A skin lesion imaged with a dermatoscope: 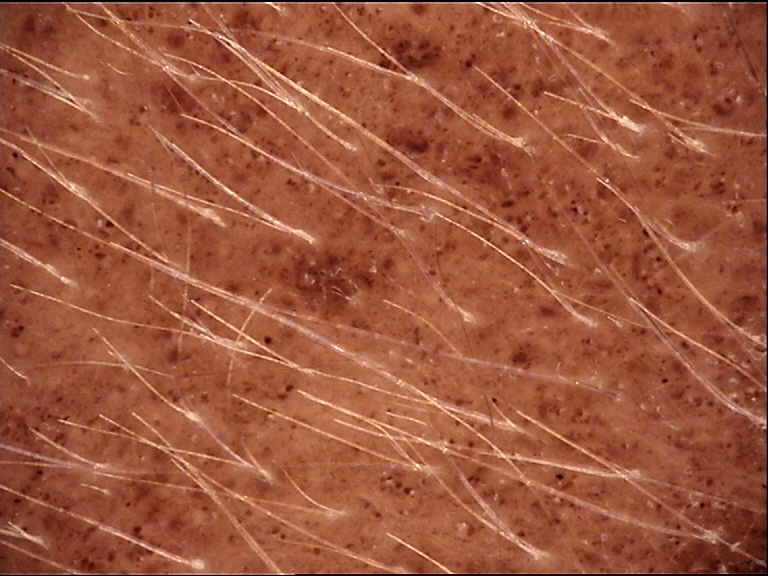– classification: banal
– diagnostic label: congenital junctional nevus (expert consensus)